A dermoscopic image of a skin lesion.
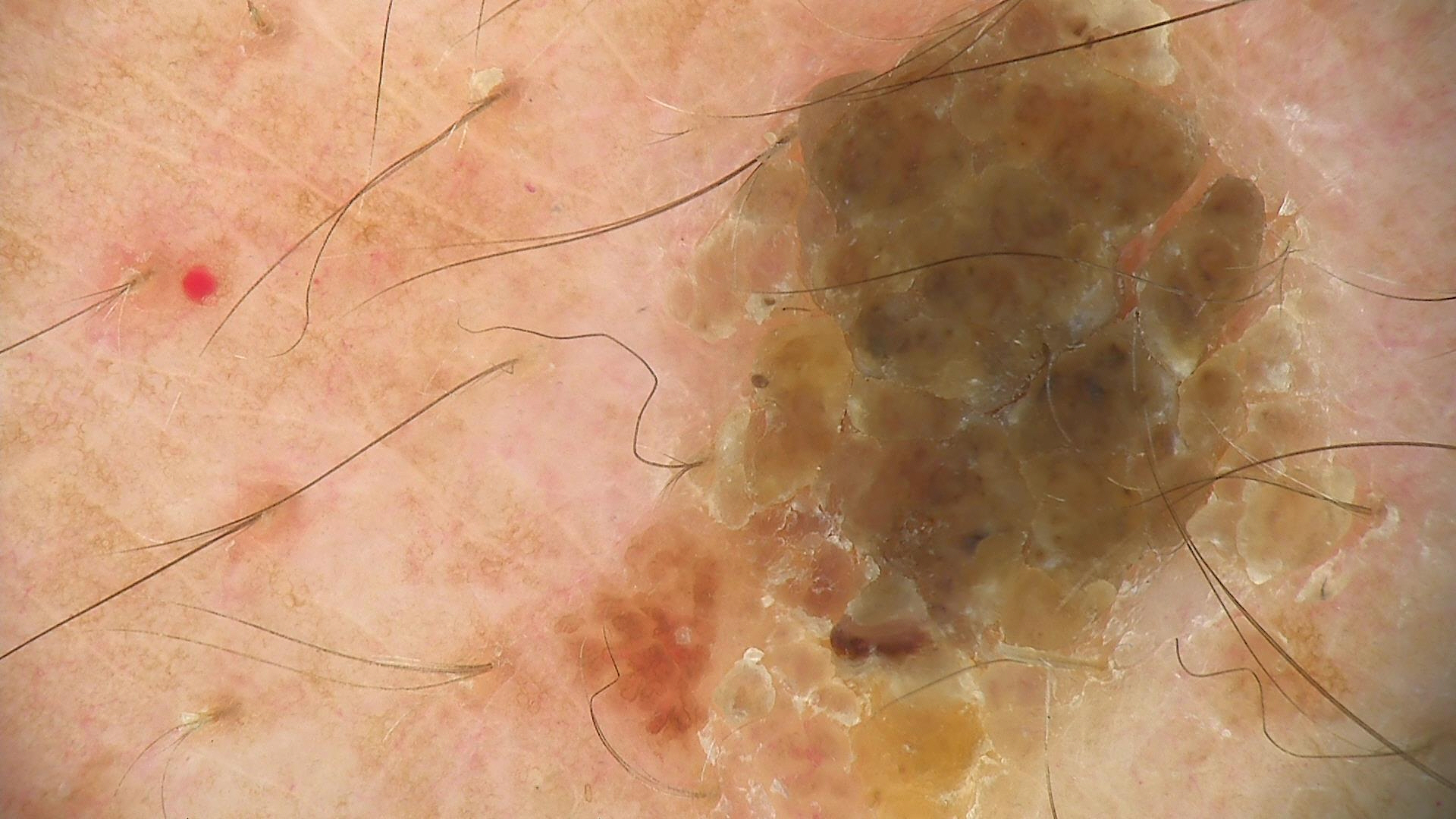<lesion>
  <lesion_type>
    <main_class>keratinocytic</main_class>
  </lesion_type>
  <diagnosis>
    <name>seborrheic keratosis</name>
    <code>sk</code>
    <malignancy>benign</malignancy>
    <super_class>non-melanocytic</super_class>
    <confirmation>expert consensus</confirmation>
  </diagnosis>
</lesion>